The patient is a female aged 30–39 · a close-up photograph · the arm is involved — 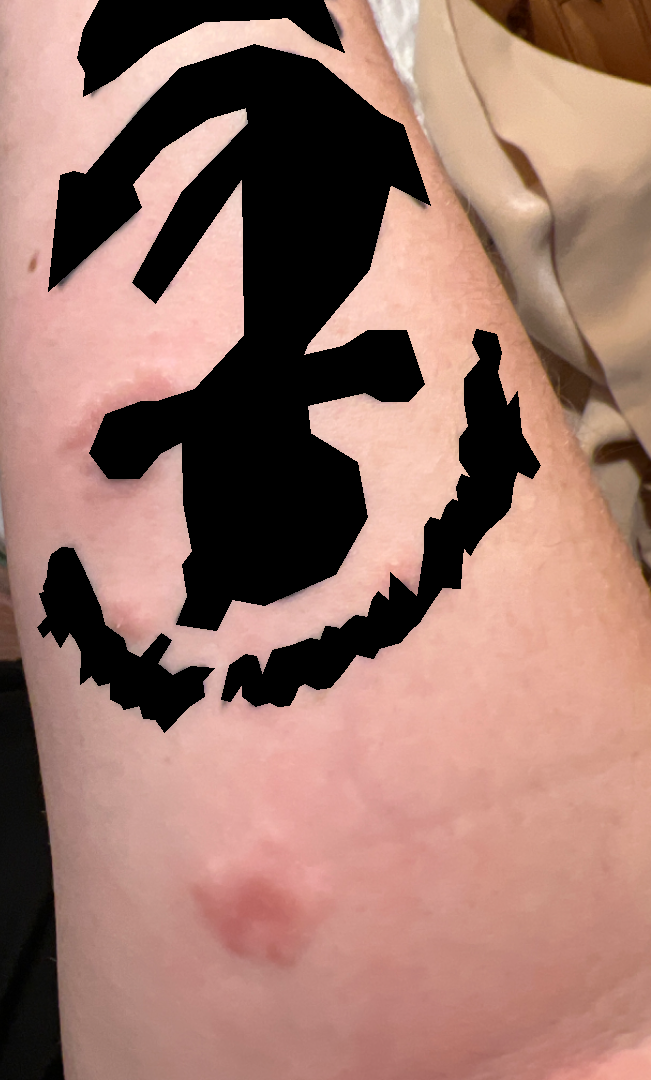Case summary:
- differential diagnosis · Cutaneous sarcoidosis (possible); Allergic Contact Dermatitis (possible)